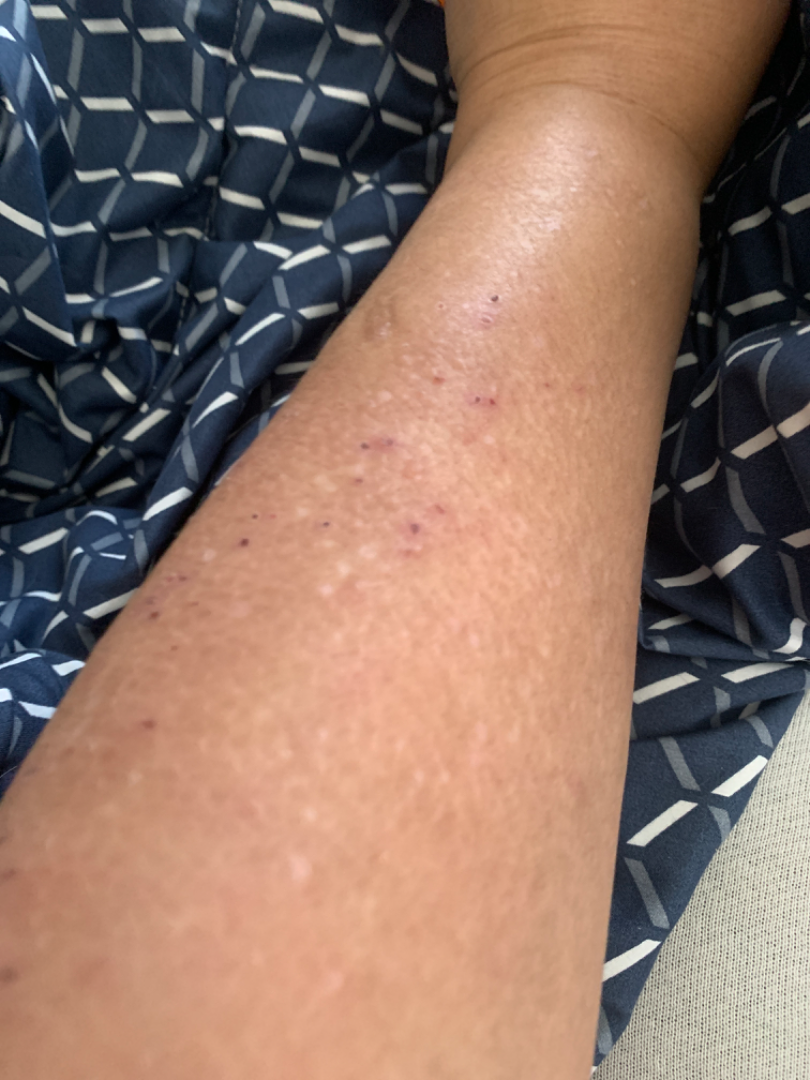| feature | finding |
|---|---|
| assessment | unable to determine |
| reported symptoms | itching |
| affected area | arm |
| lesion texture | raised or bumpy, rough or flaky and flat |
| onset | less than one week |
| image framing | close-up |
| patient describes the issue as | a rash |